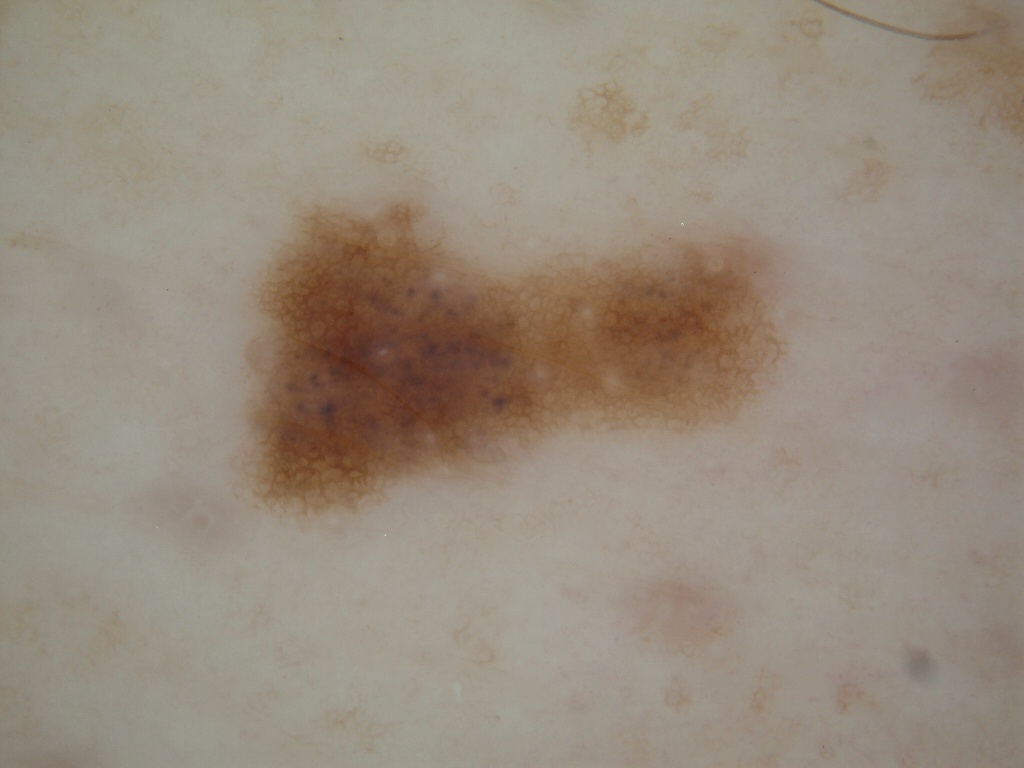  image:
    modality: dermoscopy
  lesion_location:
    bbox_xyxy:
      - 237
      - 195
      - 786
      - 518
  dermoscopic_features:
    present:
      - milia-like cysts
      - pigment network
    absent:
      - globules
      - streaks
      - negative network
  diagnosis:
    name: melanocytic nevus
    malignancy: benign
    lineage: melanocytic
    provenance: clinical